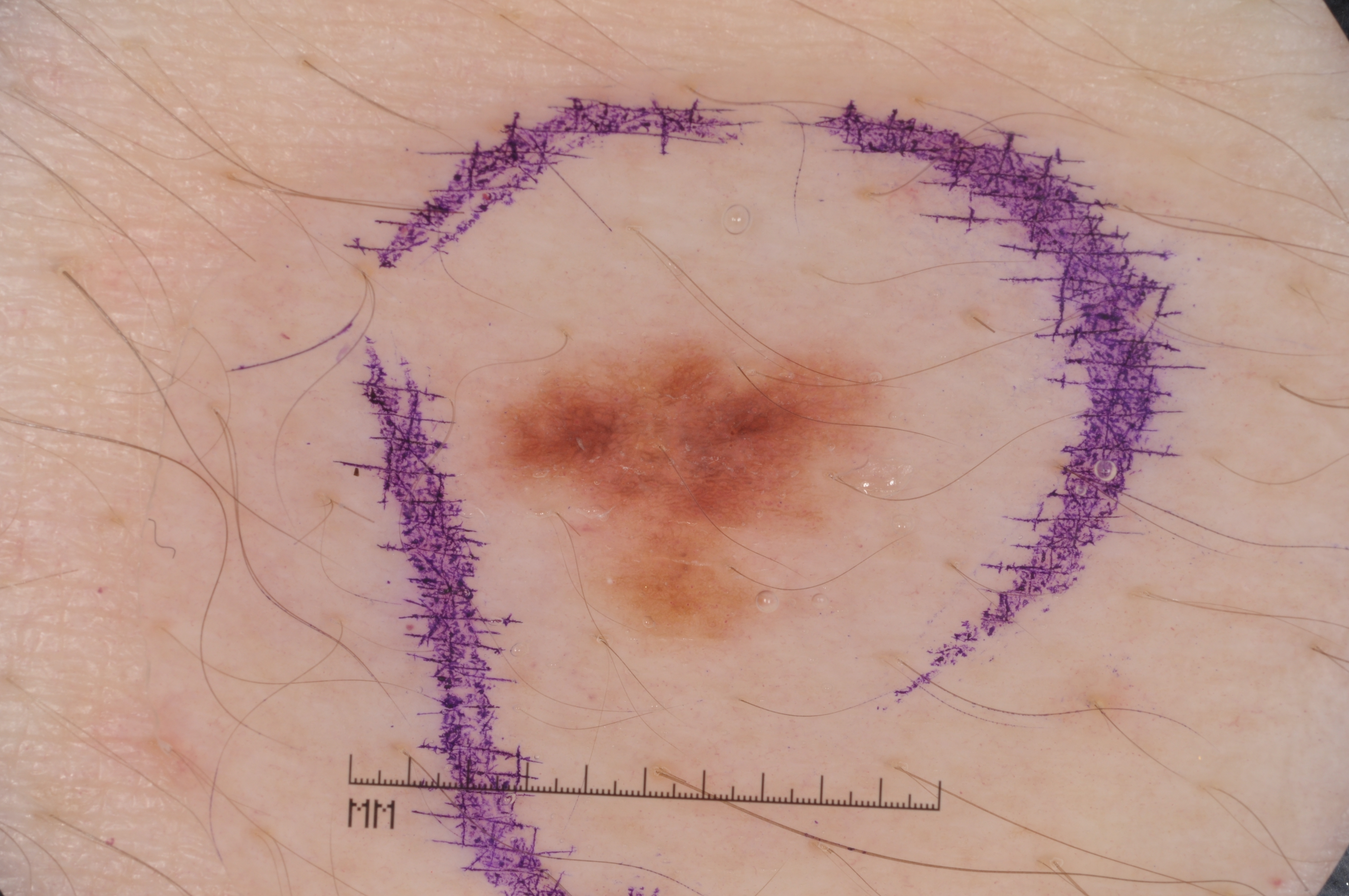subject: male, about 45 years old; imaging: dermoscopy of a skin lesion; bounding box: x1=467, y1=314, x2=924, y2=679; extent: ~10% of the field; dermoscopic features: pigment network; assessment: a melanocytic nevus.